The patient is a male roughly 55 years of age · a dermoscopic view of a skin lesion — 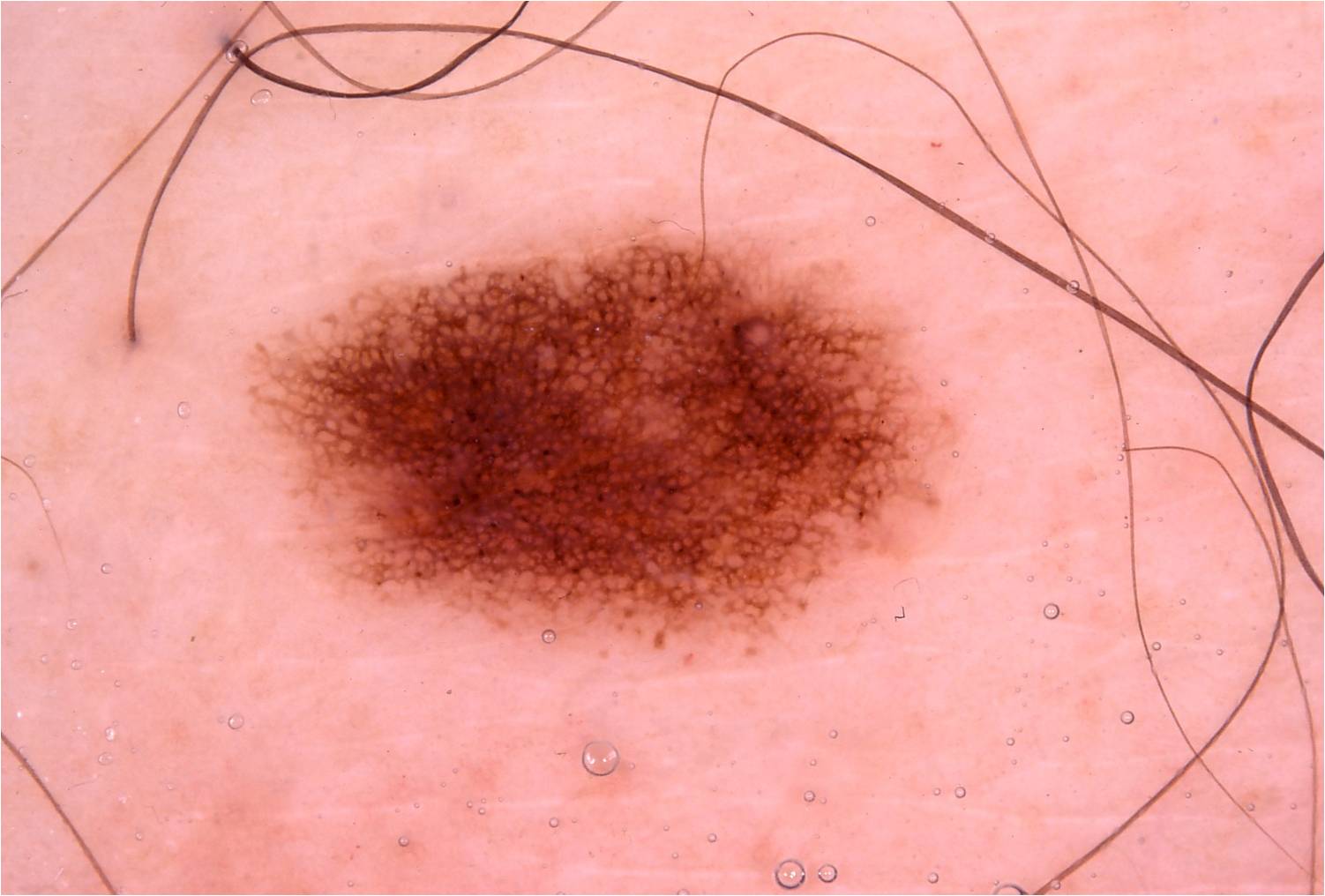Image and clinical context:
The visible lesion spans [232,202,993,676]. Dermoscopic examination shows pigment network and globules, with no negative network, milia-like cysts, or streaks. A mid-sized lesion within the field.
Conclusion:
The clinical diagnosis was a melanocytic nevus.